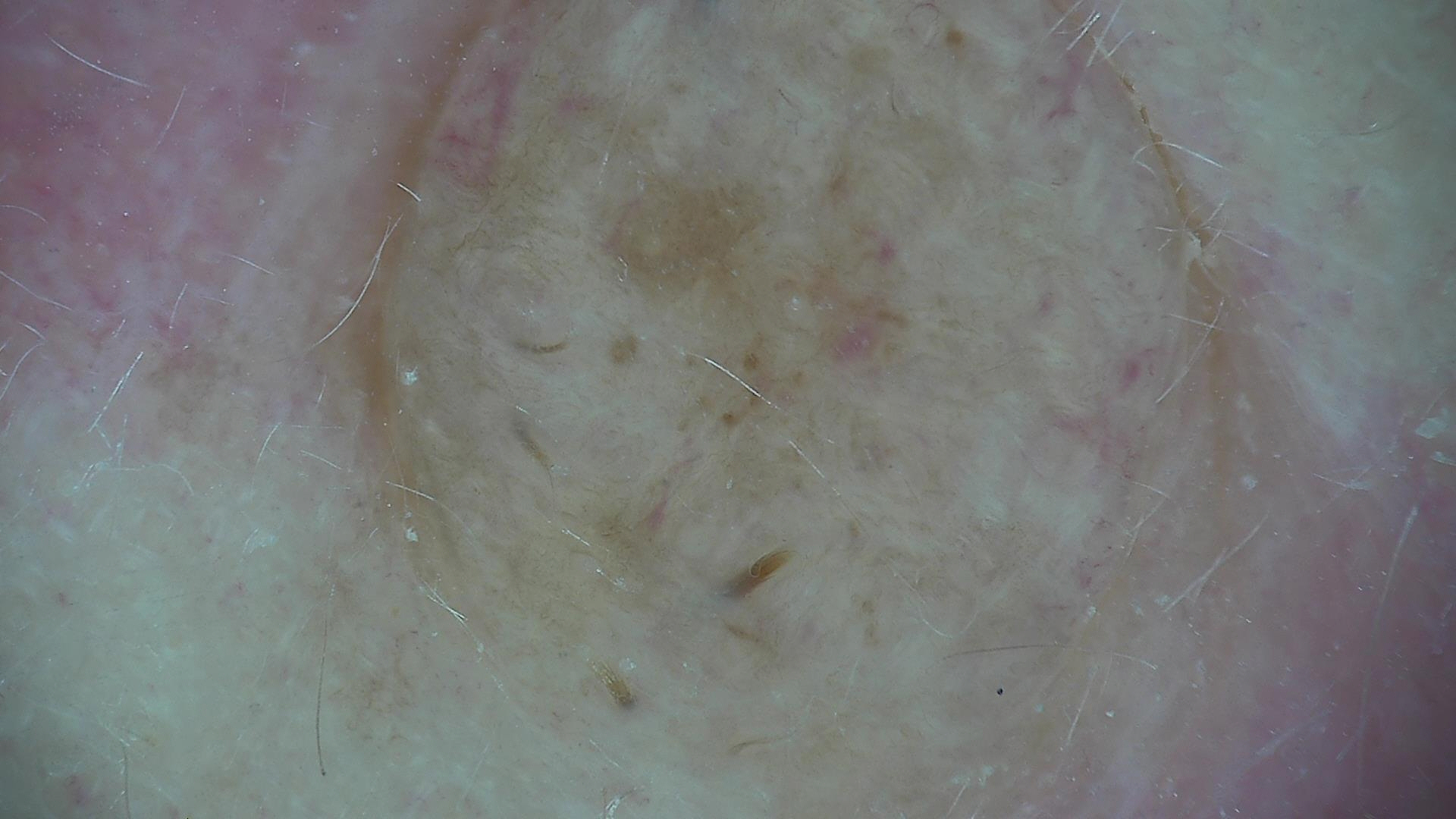Q: What is the lesion category?
A: banal
Q: What is this lesion?
A: dermal nevus (expert consensus)